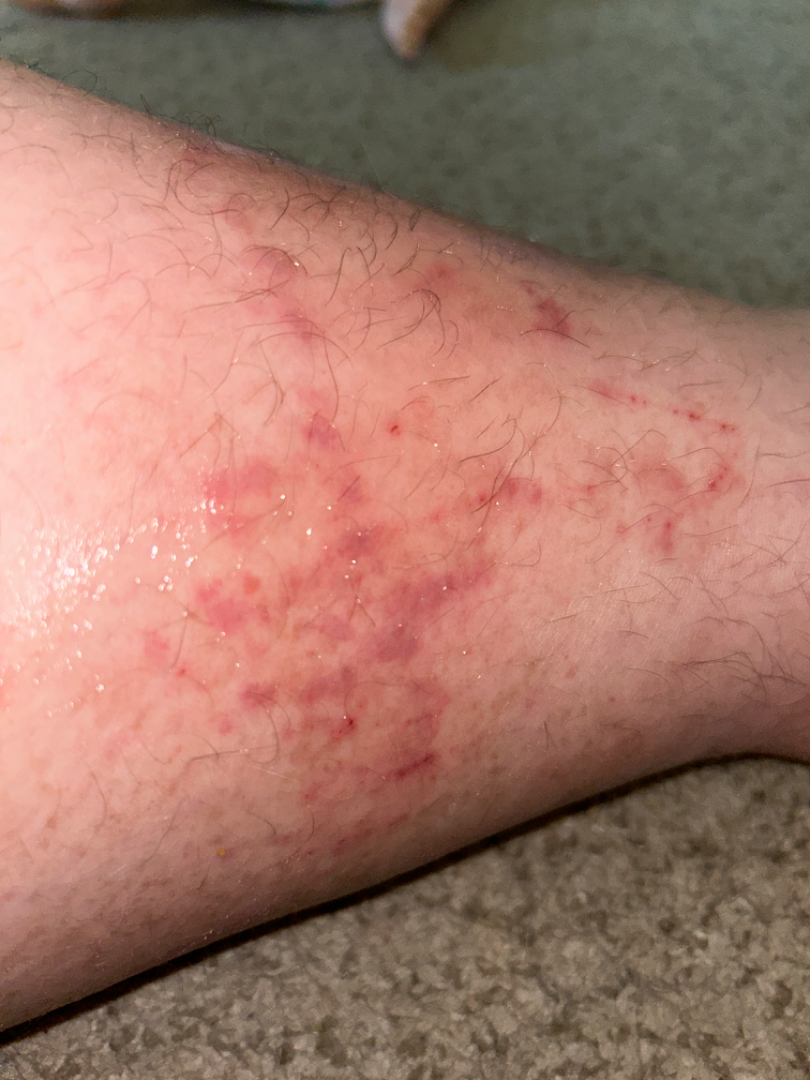diagnostic considerations: Allergic Contact Dermatitis (100%).